The photo was captured at a distance. Female subject, age 18–29.
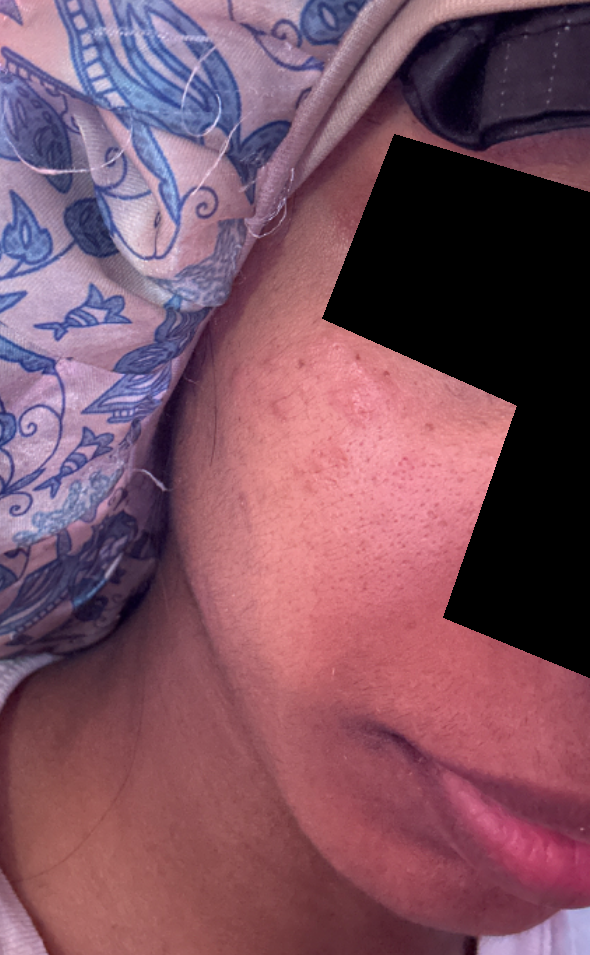<case>
  <differential>Acne, Rosacea</differential>
</case>